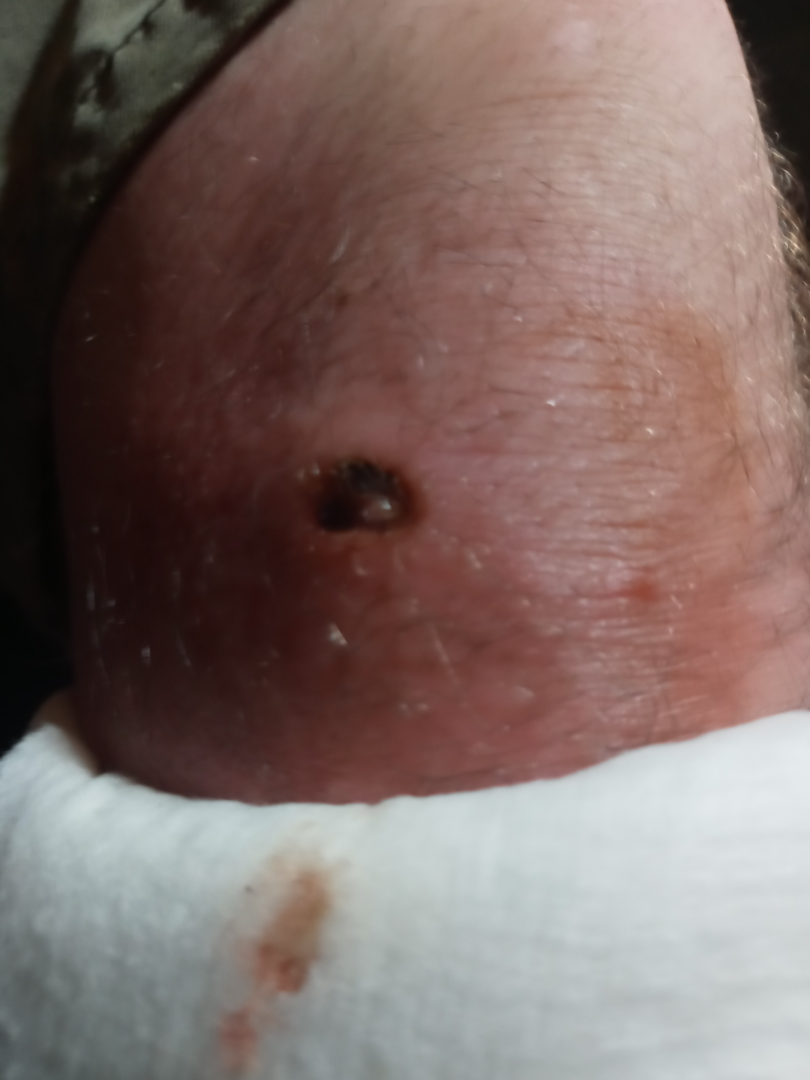On remote dermatologist review, favoring Ecthyma; an alternative is Abrasion, scrape, or scab; with consideration of Abscess.